A dermoscopic close-up of a skin lesion.
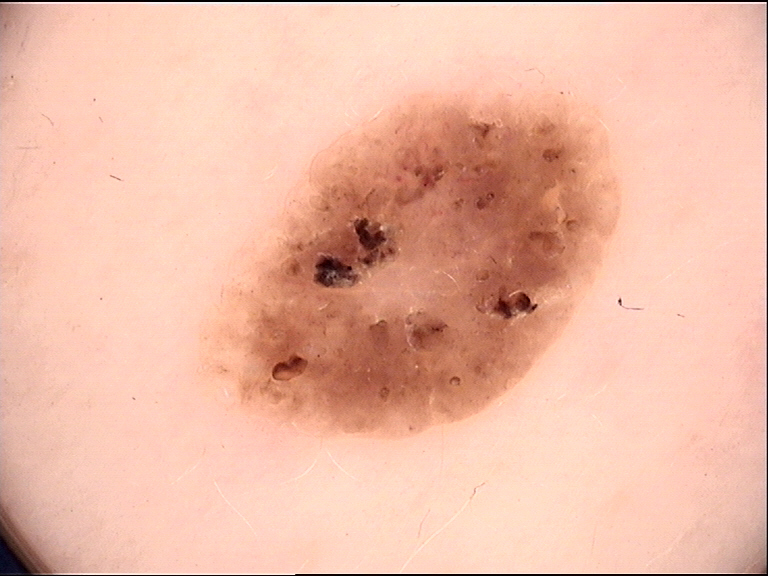diagnosis:
  name: seborrheic keratosis
  code: sk
  malignancy: benign
  super_class: non-melanocytic
  confirmation: expert consensus